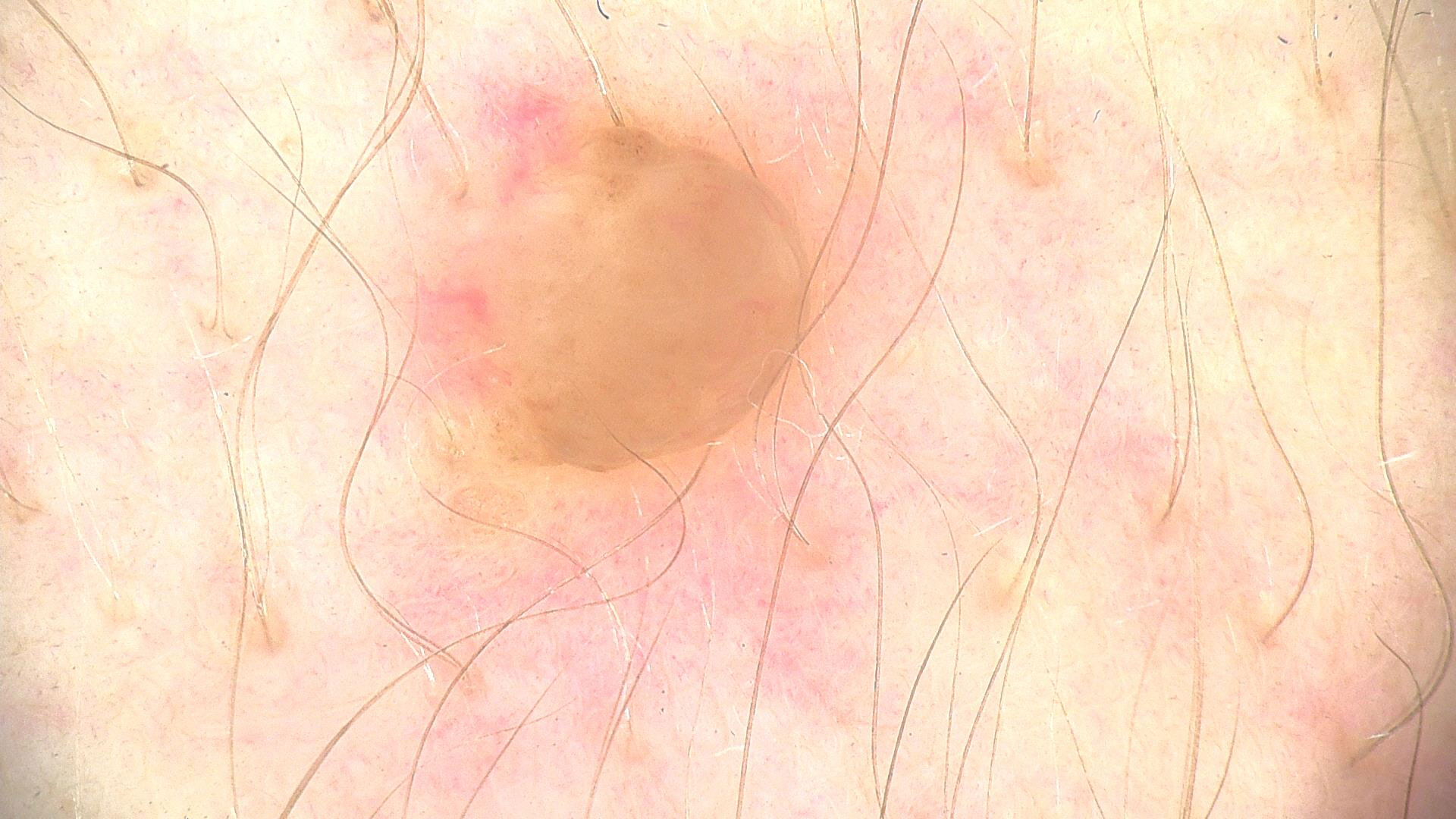Case:
- subtype · banal
- diagnostic label · dermal nevus (expert consensus)